A skin lesion imaged with a dermatoscope.
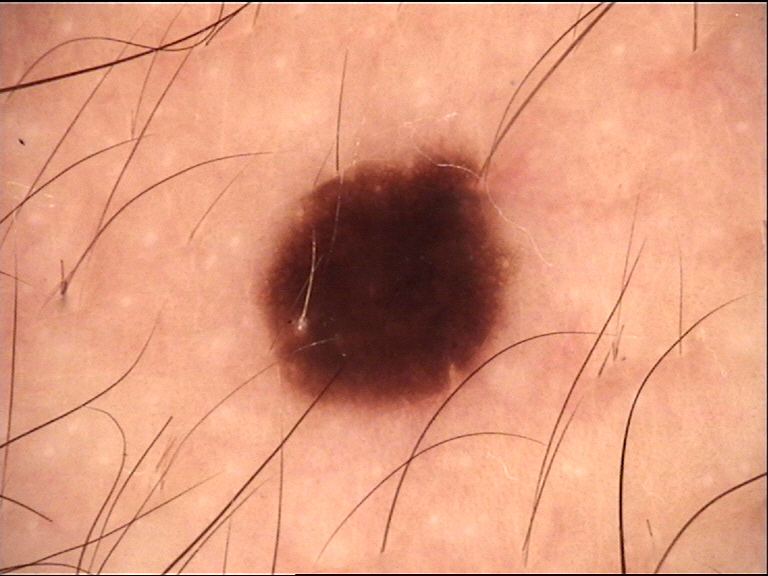Conclusion: The diagnostic label was a banal lesion — a junctional nevus.